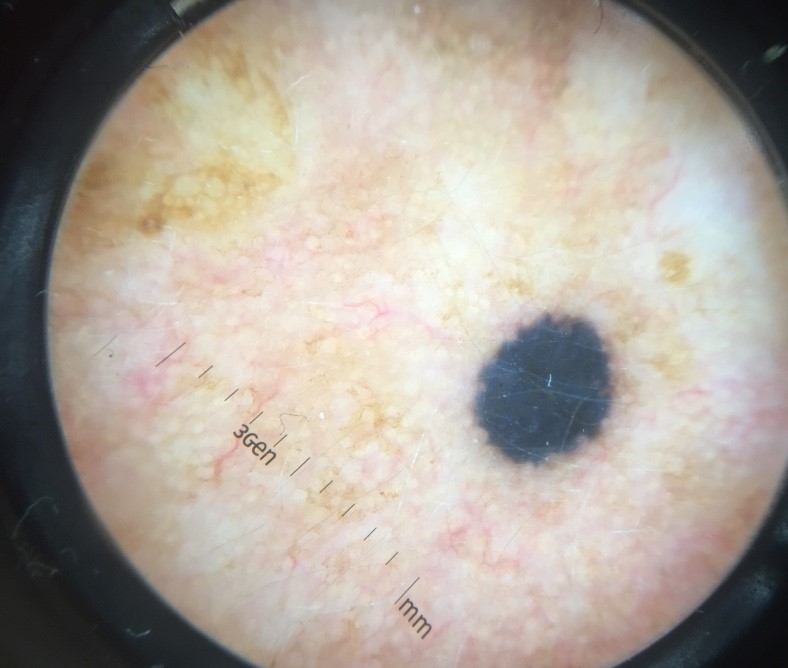assessment — blue nevus (expert consensus).